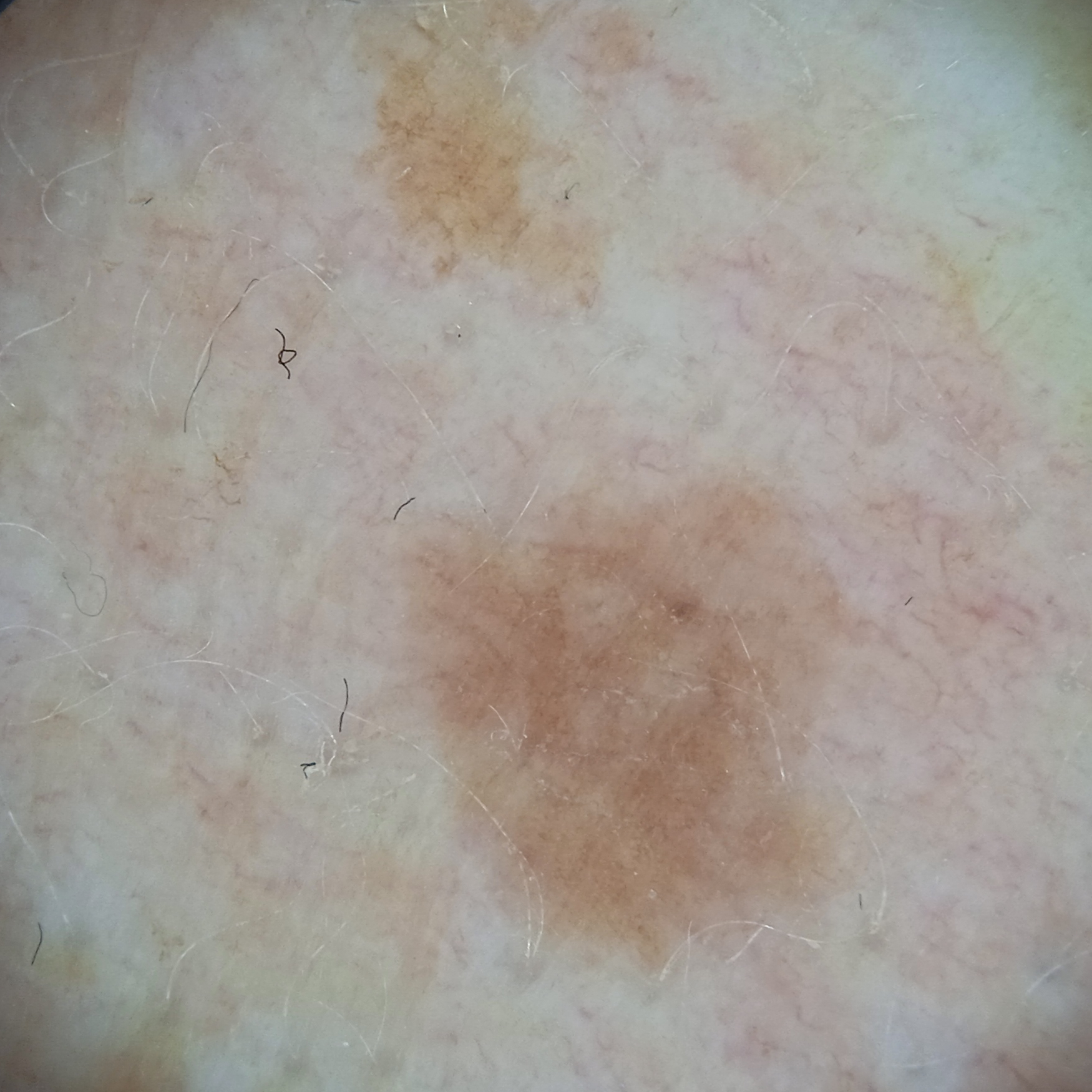  patient:
    age: 59
    sex: female
  image: dermoscopic image
  lesion_location: an arm
  lesion_size:
    diameter_mm: 6.5
  diagnosis:
    name: melanocytic nevus
    malignancy: benign